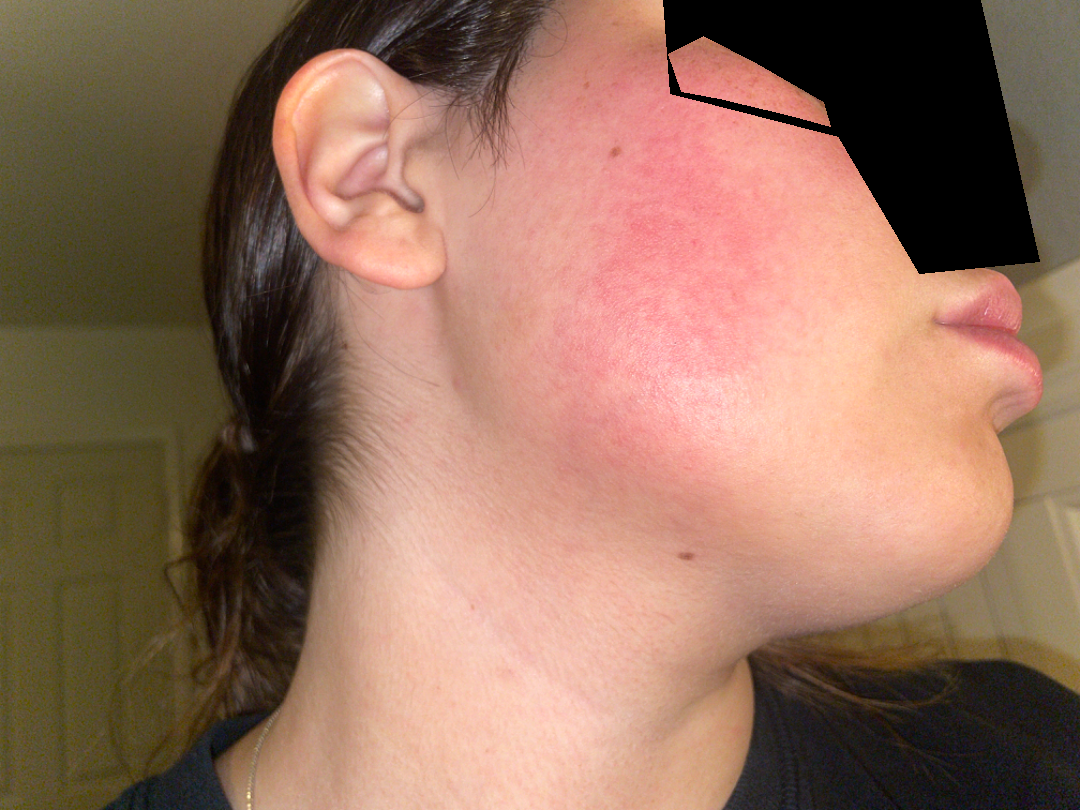Notes:
- assessment — not assessable
- constitutional symptoms — chills
- lesion texture — flat
- onset — about one day
- reported symptoms — bothersome appearance, burning and enlargement
- patient's own categorization — a rash
- framing — at an angle